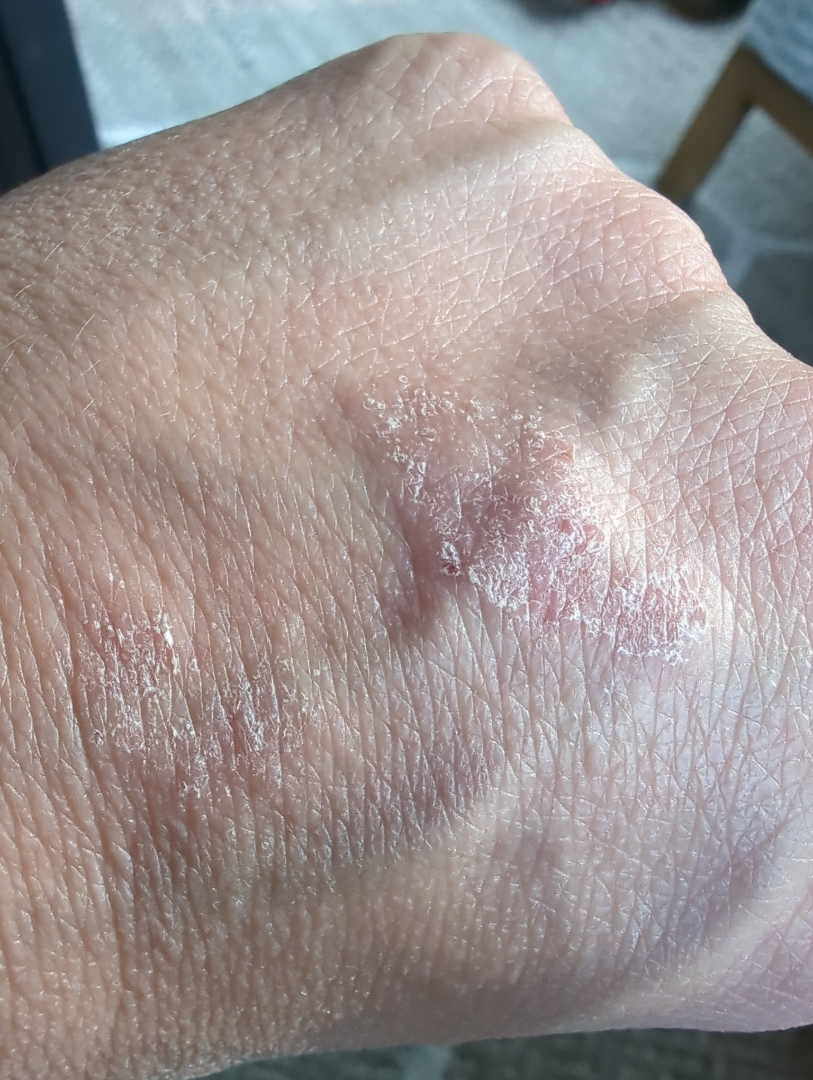{"skin_tone": {"fitzpatrick": "II", "monk_skin_tone": [2, 3]}, "systemic_symptoms": "none reported", "patient_category": "a rash", "shot_type": "close-up", "duration": "one to four weeks", "symptoms": "enlargement", "patient": "female, age 40–49", "body_site": "back of the hand", "differential": {"Psoriasis": 0.35, "Eczema": 0.35, "Contact dermatitis": 0.23, "Tinea": 0.08}}